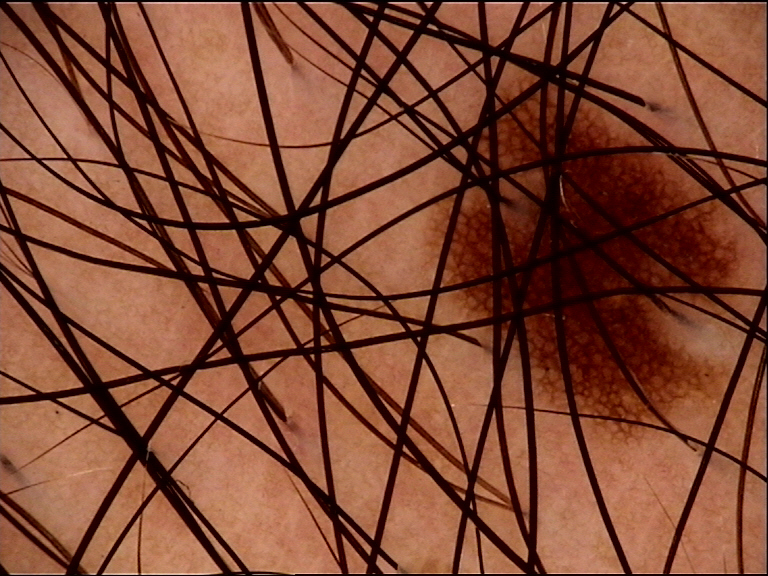Conclusion:
The diagnostic label was a junctional nevus.